The subject is a female aged 50–59 · located on the palm, arm and back of the hand · self-categorized by the patient as a rash · texture is reported as fluid-filled and raised or bumpy · close-up view · the patient also reports fatigue · the lesion is associated with enlargement, burning, pain and bothersome appearance · skin tone: FST II.
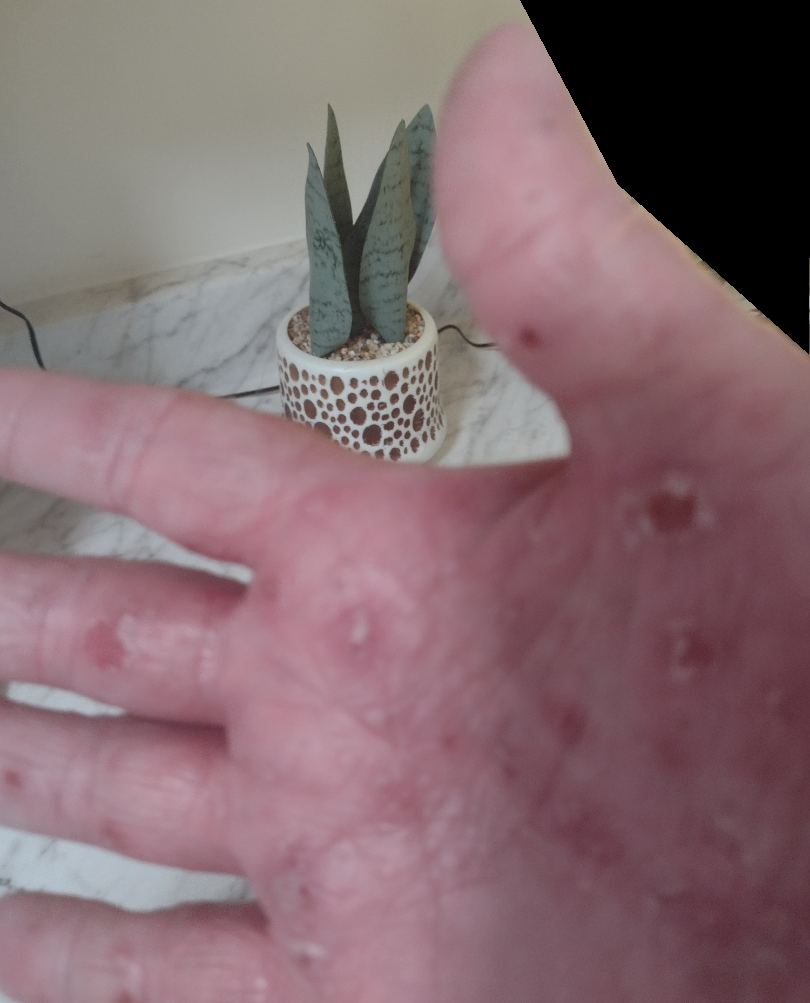Most consistent with Syphilis.